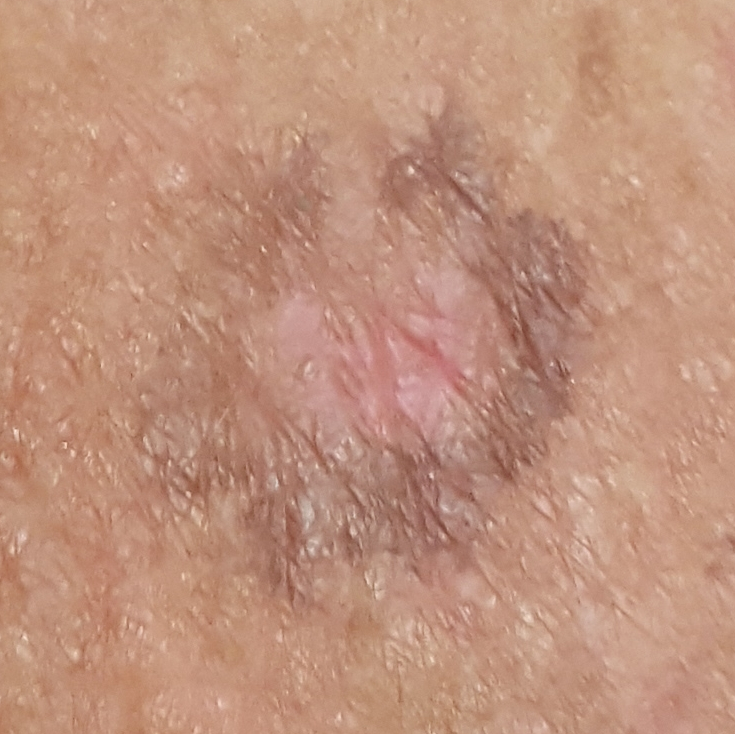A female subject 57 years old. A clinical photograph of a skin lesion. The lesion is on the chest. The patient reports that the lesion itches, but has not bled and has not grown. On biopsy, the diagnosis was an actinic keratosis.